A male subject about 60 years old, a dermatoscopic image of a skin lesion — 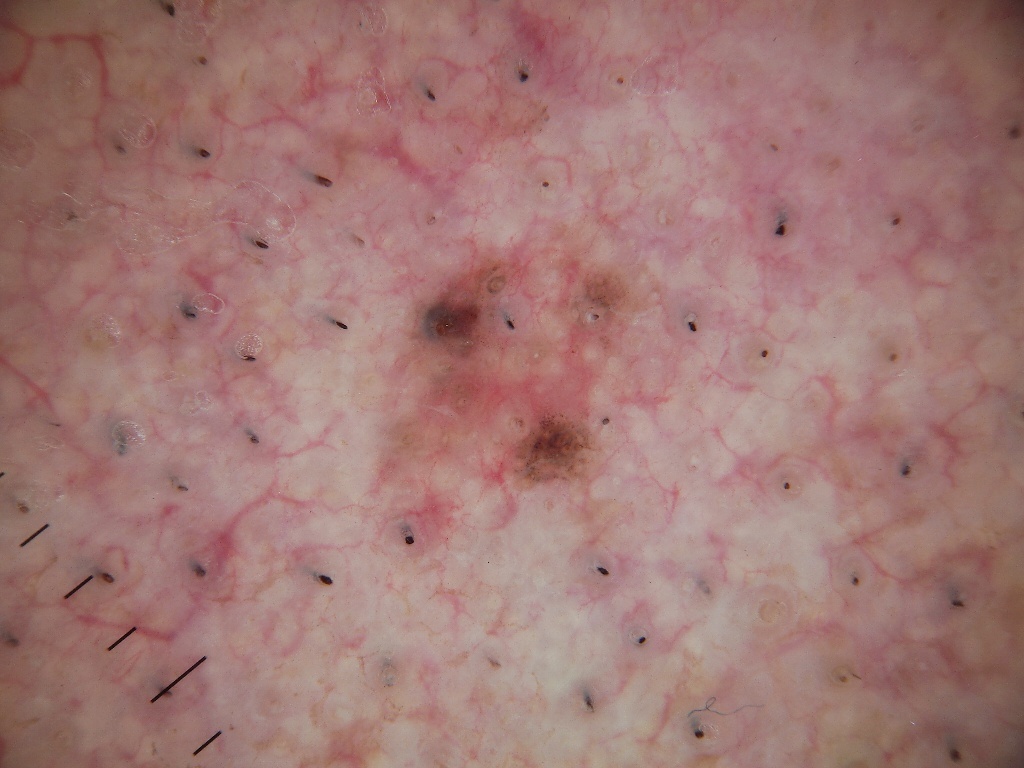Dermoscopy demonstrates globules.
The lesion spans x1=342 y1=219 x2=671 y2=582.
The lesion takes up a moderate portion of the field.
On biopsy, the diagnosis was a melanoma.